A dermoscopy image of a single skin lesion:
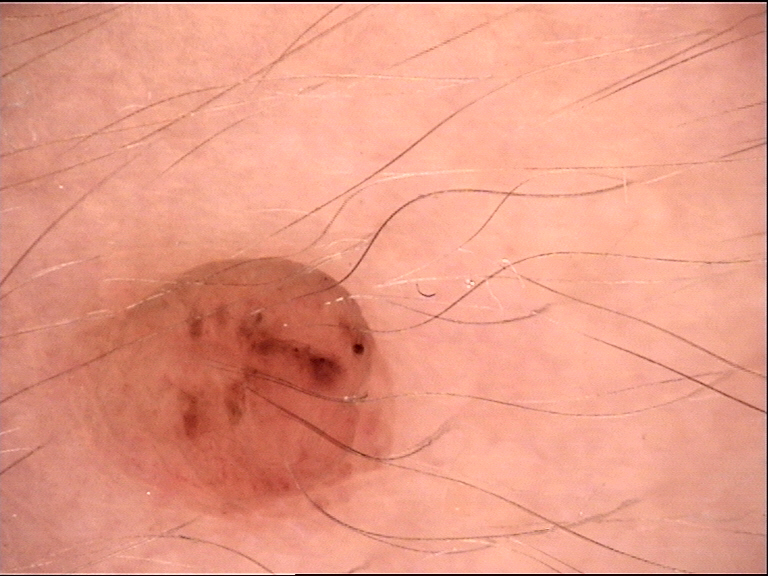This is a banal lesion.
Consistent with a dermal nevus.